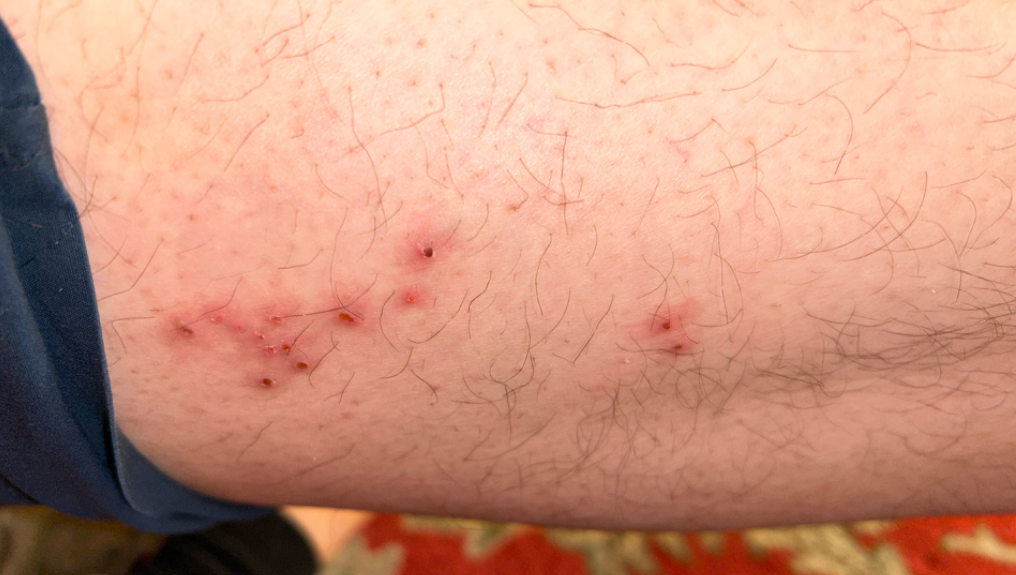Notes:
– skin tone · Fitzpatrick skin type IV
– shot type · at an angle
– impression · the leading consideration is Herpes Zoster; also consider Impetigo